A dermatoscopic image of a skin lesion:
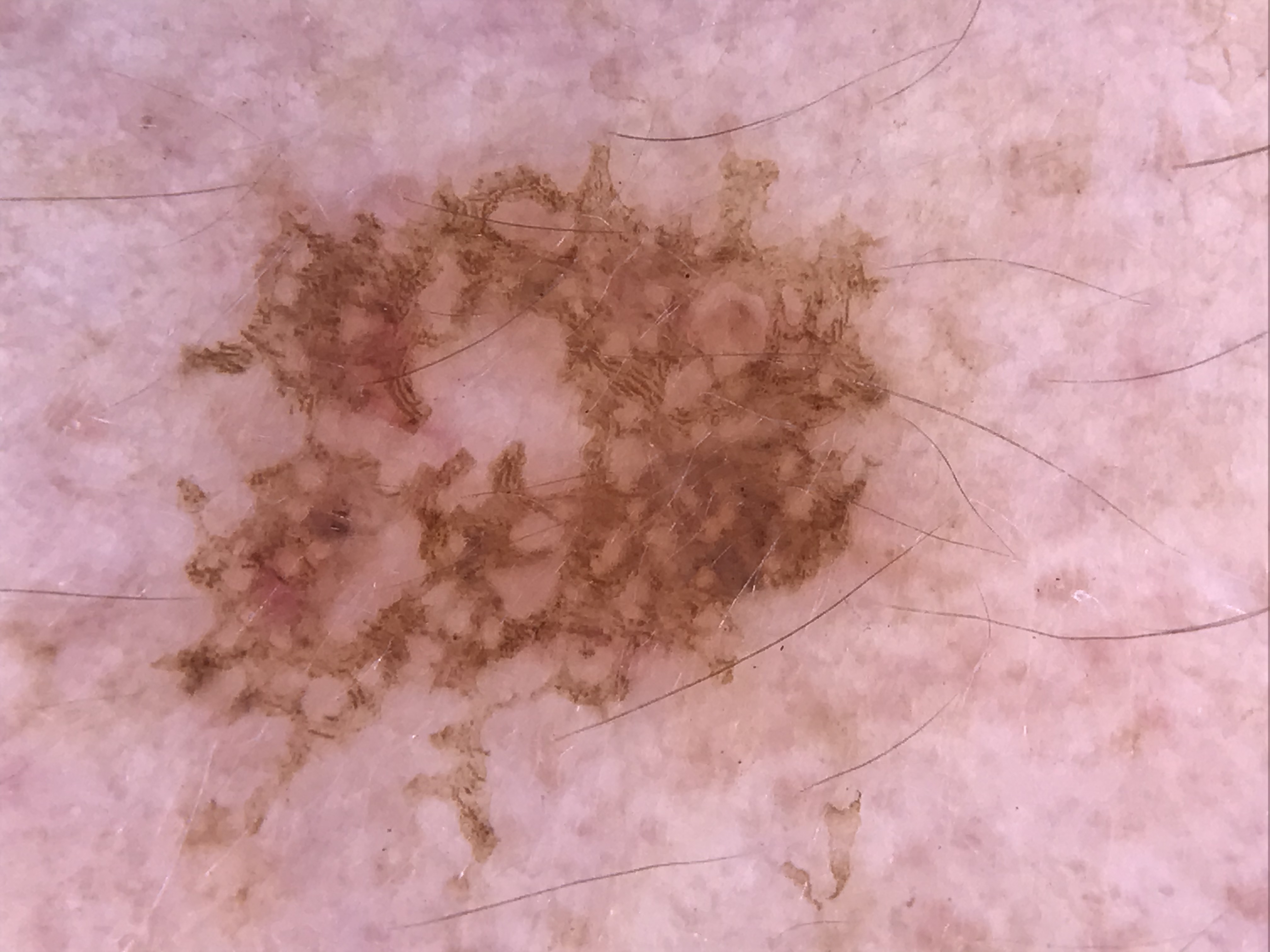Findings: The architecture is that of a keratinocytic lesion. Conclusion: The diagnostic label was a seborrheic keratosis.